The photo was captured at an angle — 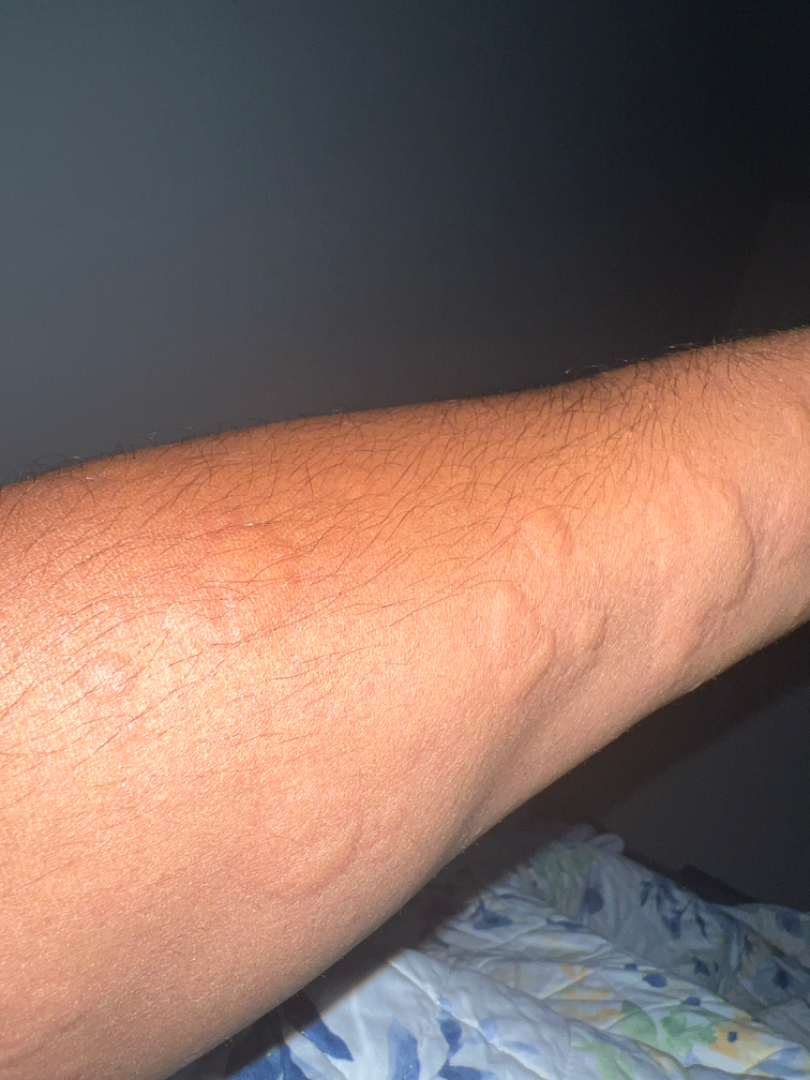<dermatology_case>
<differential>
  <leading>Urticaria</leading>
  <considered>Insect Bite, Allergic Contact Dermatitis</considered>
</differential>
</dermatology_case>